The contributor is a male aged 60–69. The contributor reports itching and bothersome appearance. The patient also reports fatigue and shortness of breath. The photograph was taken at a distance. Texture is reported as rough or flaky. The leg is involved. The contributor reports the condition has been present for more than five years.
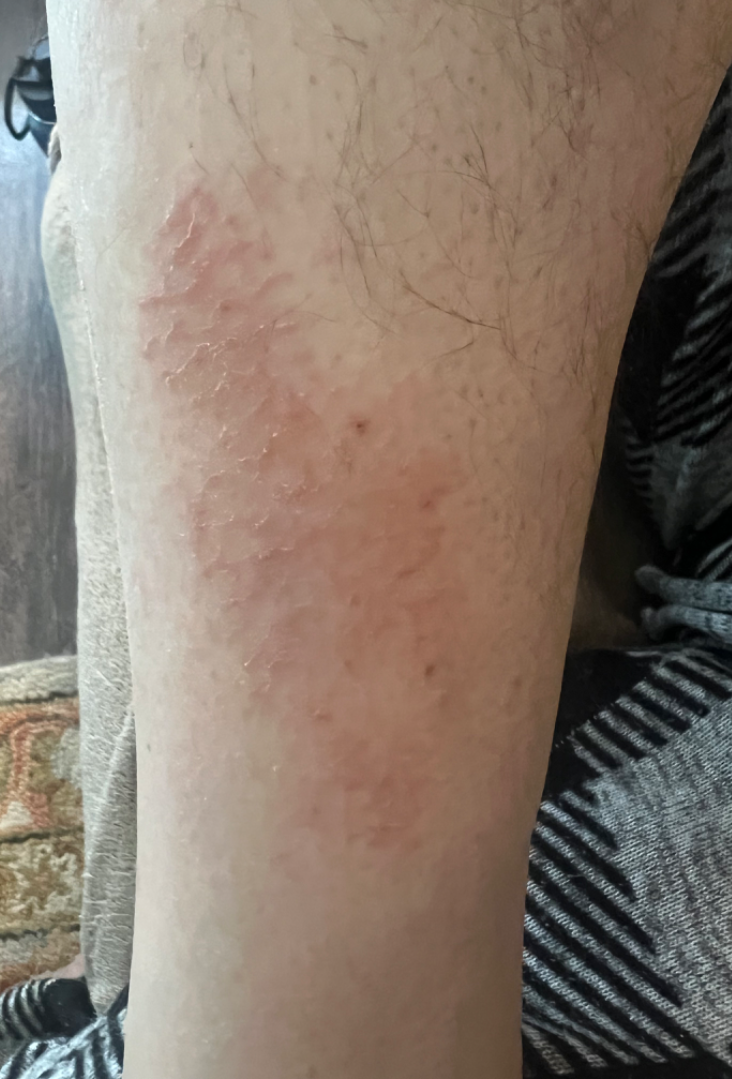On dermatologist assessment of the image, the impression is Eczema.